A skin lesion imaged with a dermatoscope · a male subject aged 48 to 52.
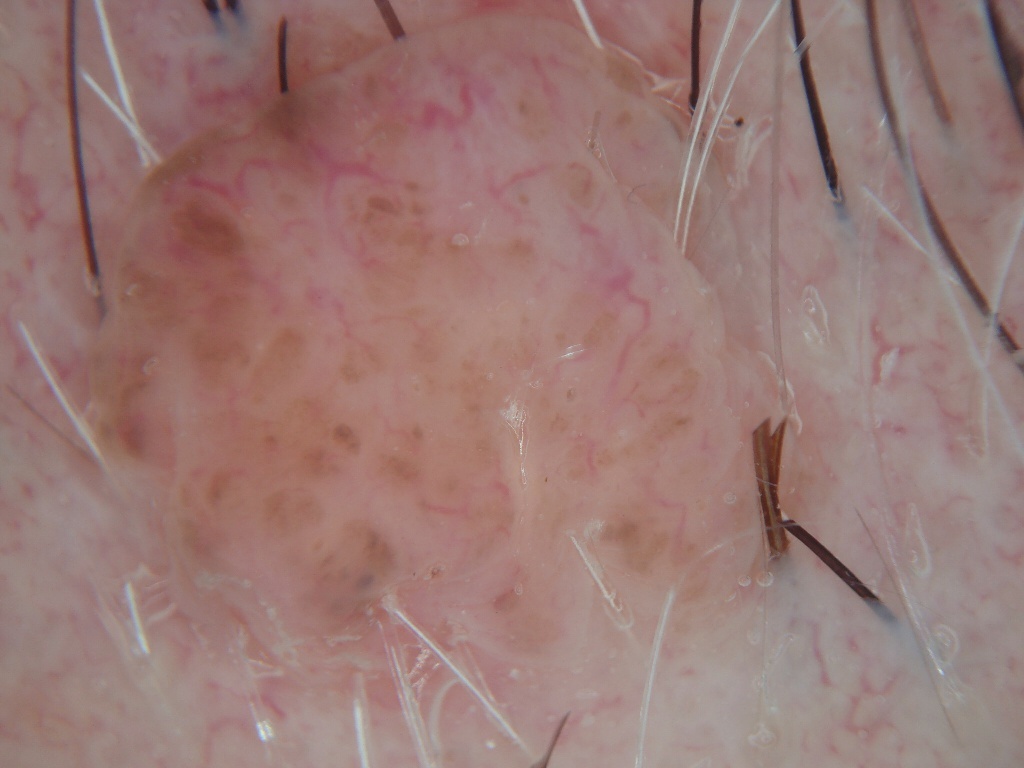Dermoscopic review identifies globules; no streaks, milia-like cysts, negative network, or pigment network. The lesion covers approximately 52% of the dermoscopic field. As (left, top, right, bottom), the lesion's extent is <bbox>77, 11, 810, 741</bbox>. Diagnosed as a melanocytic nevus.